This image was taken at a distance · non-clinician graders estimated MST 2–3.
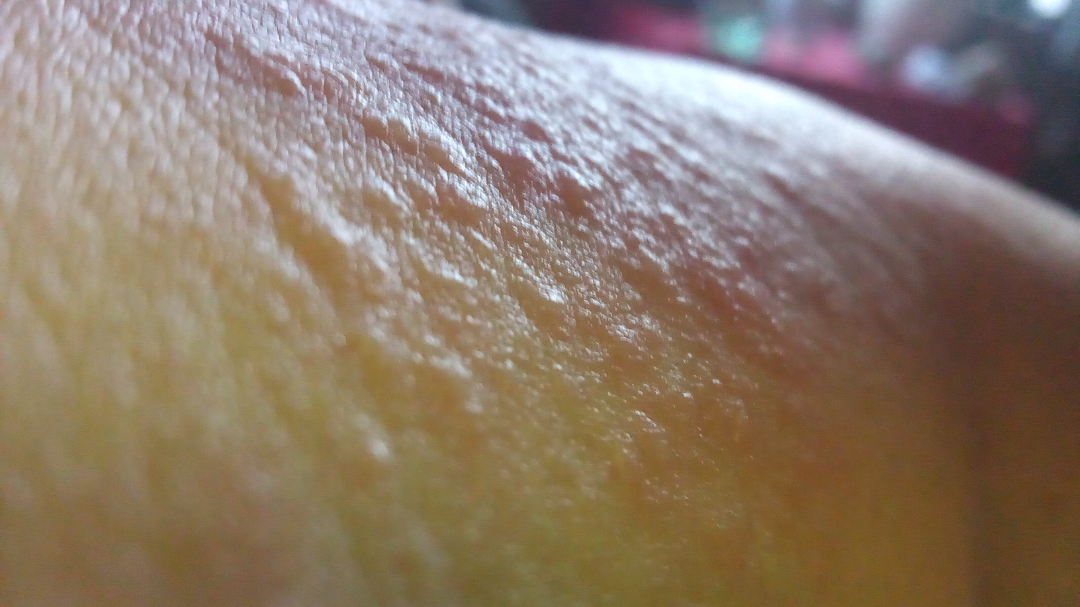The reviewing dermatologist was unable to assign a differential diagnosis from the image.